A dermoscopy image of a single skin lesion: 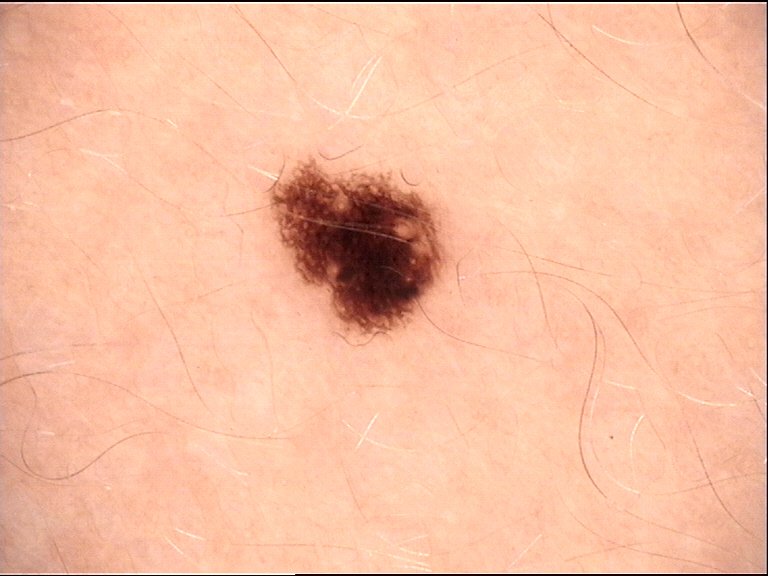The morphology is that of a banal lesion.
Classified as a junctional nevus.